The affected area is the arm; the patient is 18–29, male; this image was taken at an angle.
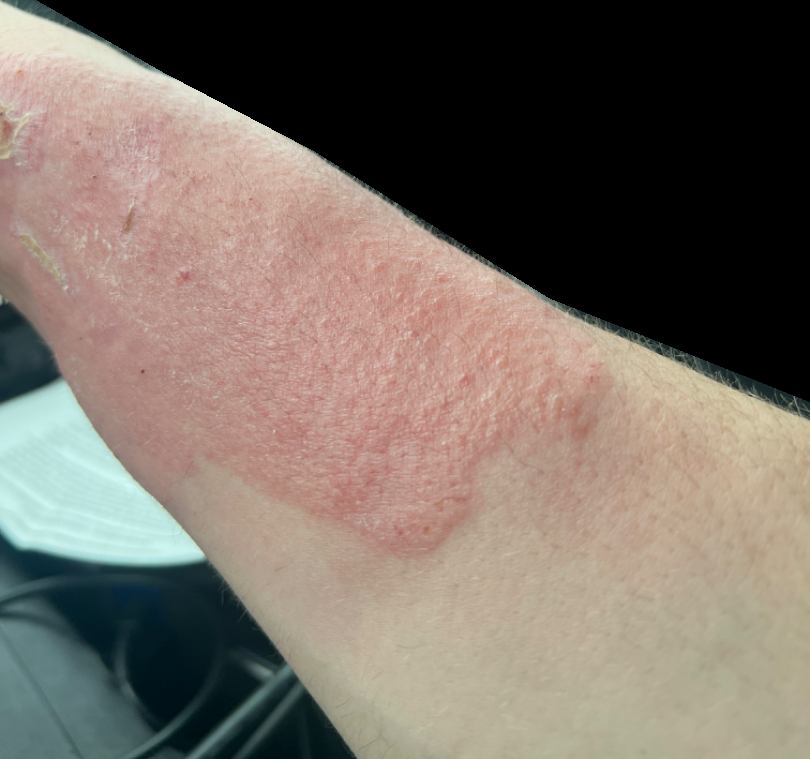patient's own categorization = a rash, described texture = raised or bumpy, symptom duration = less than one week, patient-reported symptoms = itching, dermatologist impression = the differential is split between Tinea and Allergic Contact Dermatitis.